Referred for assessment of suspected basal cell carcinoma · a female subject 64 years old — 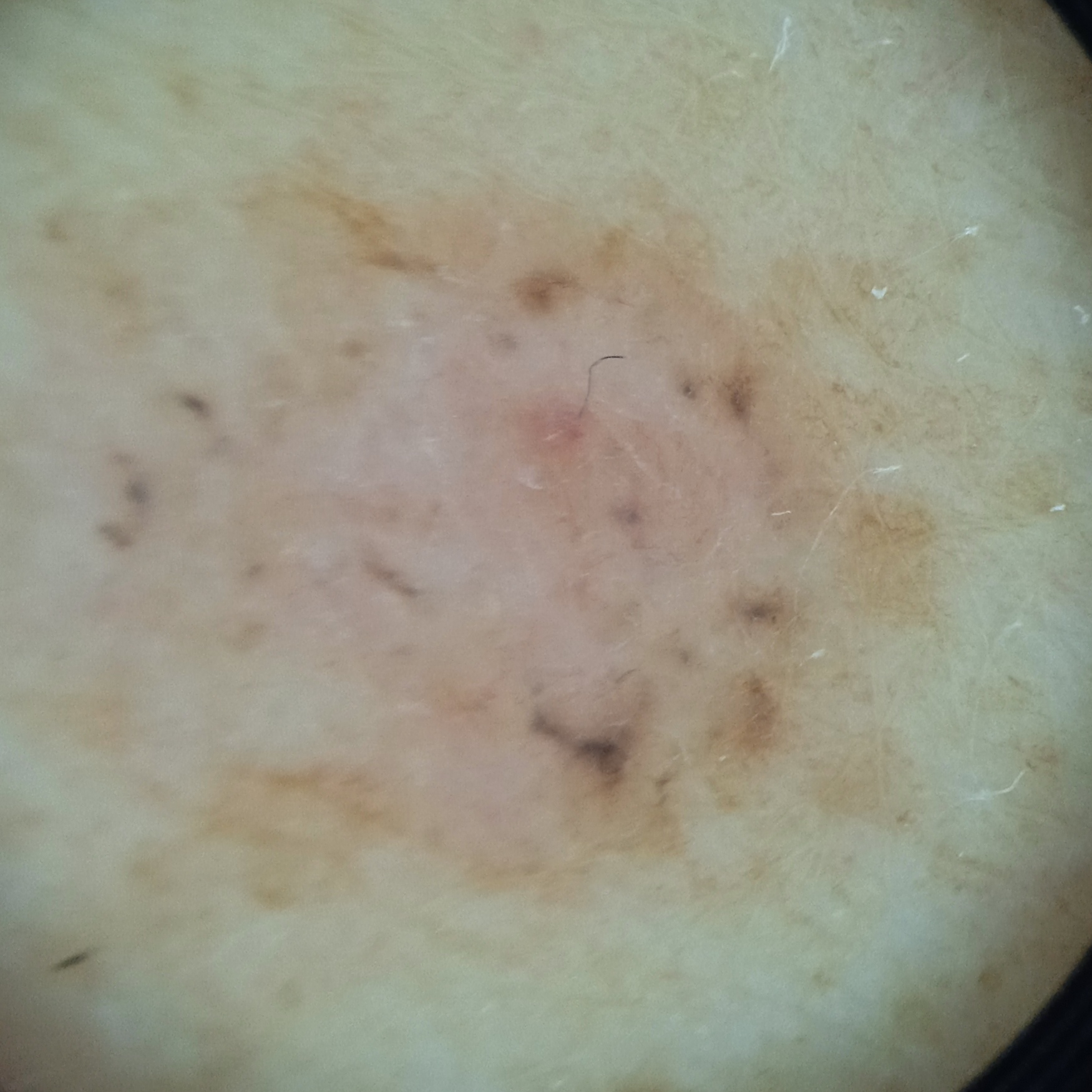| field | value |
|---|---|
| size | 9.8 mm |
| diagnostic label | basal cell carcinoma (biopsy-proven) |